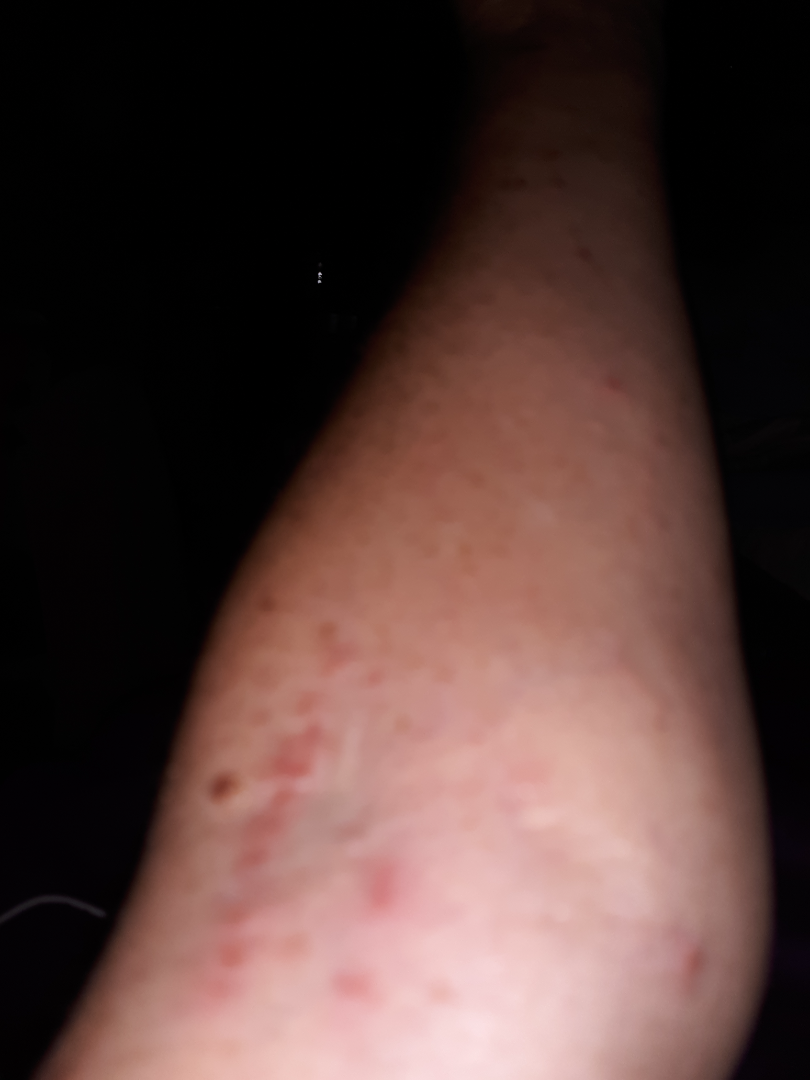skin tone = Fitzpatrick II, view = at a distance.